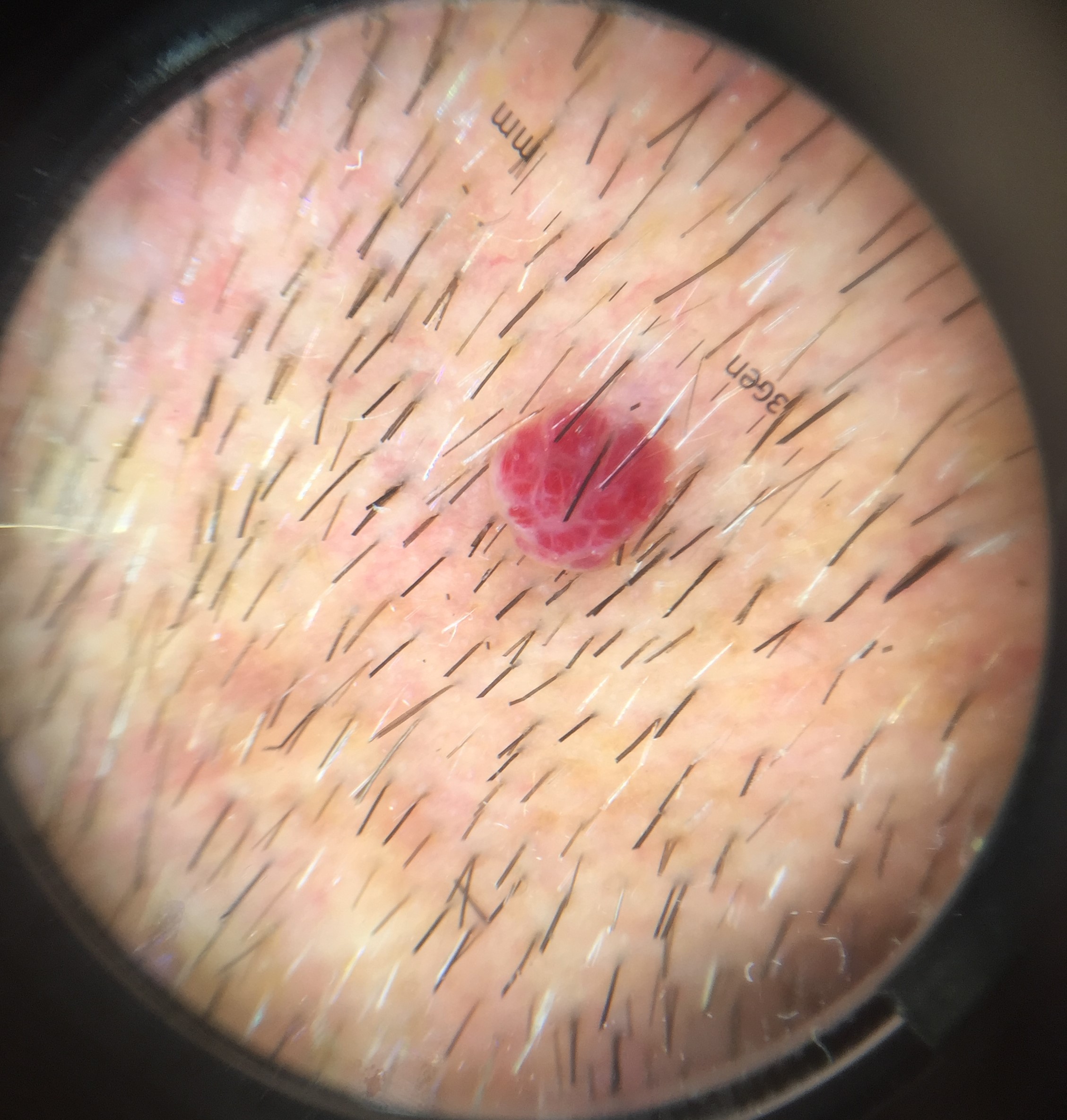Findings:
* class — hemangioma (expert consensus)